A dermatoscopic image of a skin lesion:
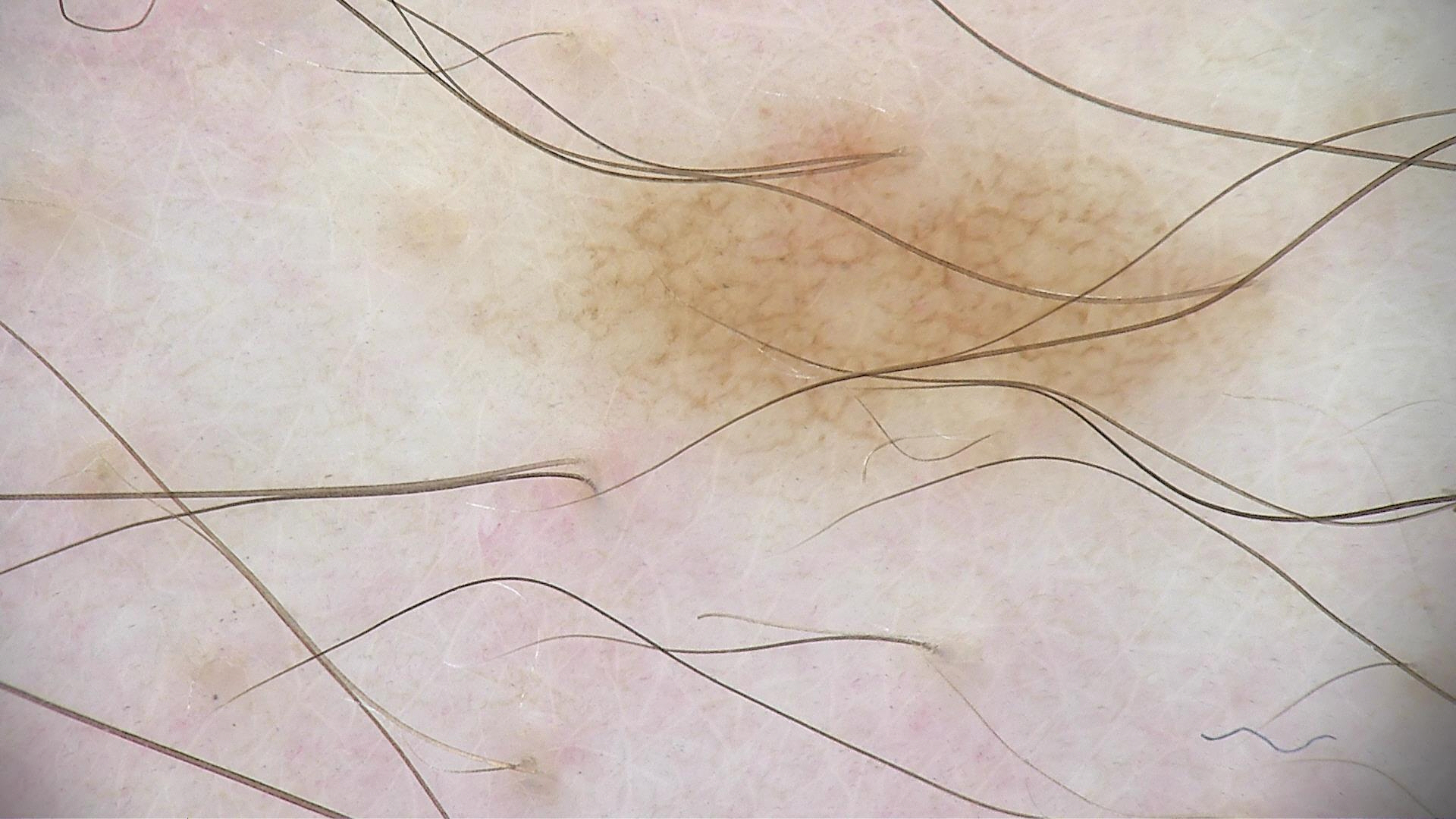Conclusion:
Consistent with a dysplastic junctional nevus.